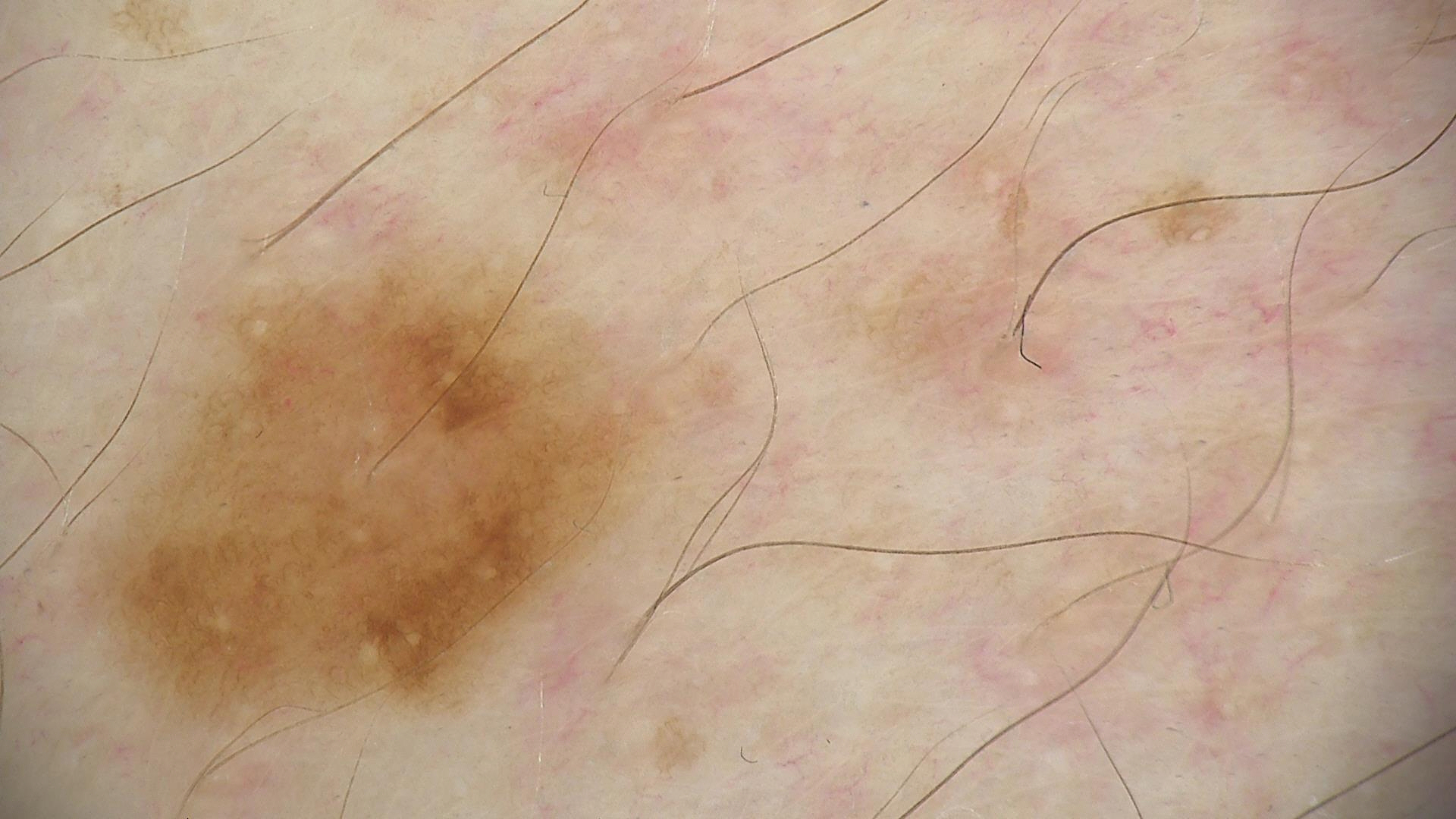<dermoscopy>
<diagnosis>
<name>dysplastic junctional nevus</name>
<code>jd</code>
<malignancy>benign</malignancy>
<super_class>melanocytic</super_class>
<confirmation>expert consensus</confirmation>
</diagnosis>
</dermoscopy>